A dermoscopic close-up of a skin lesion.
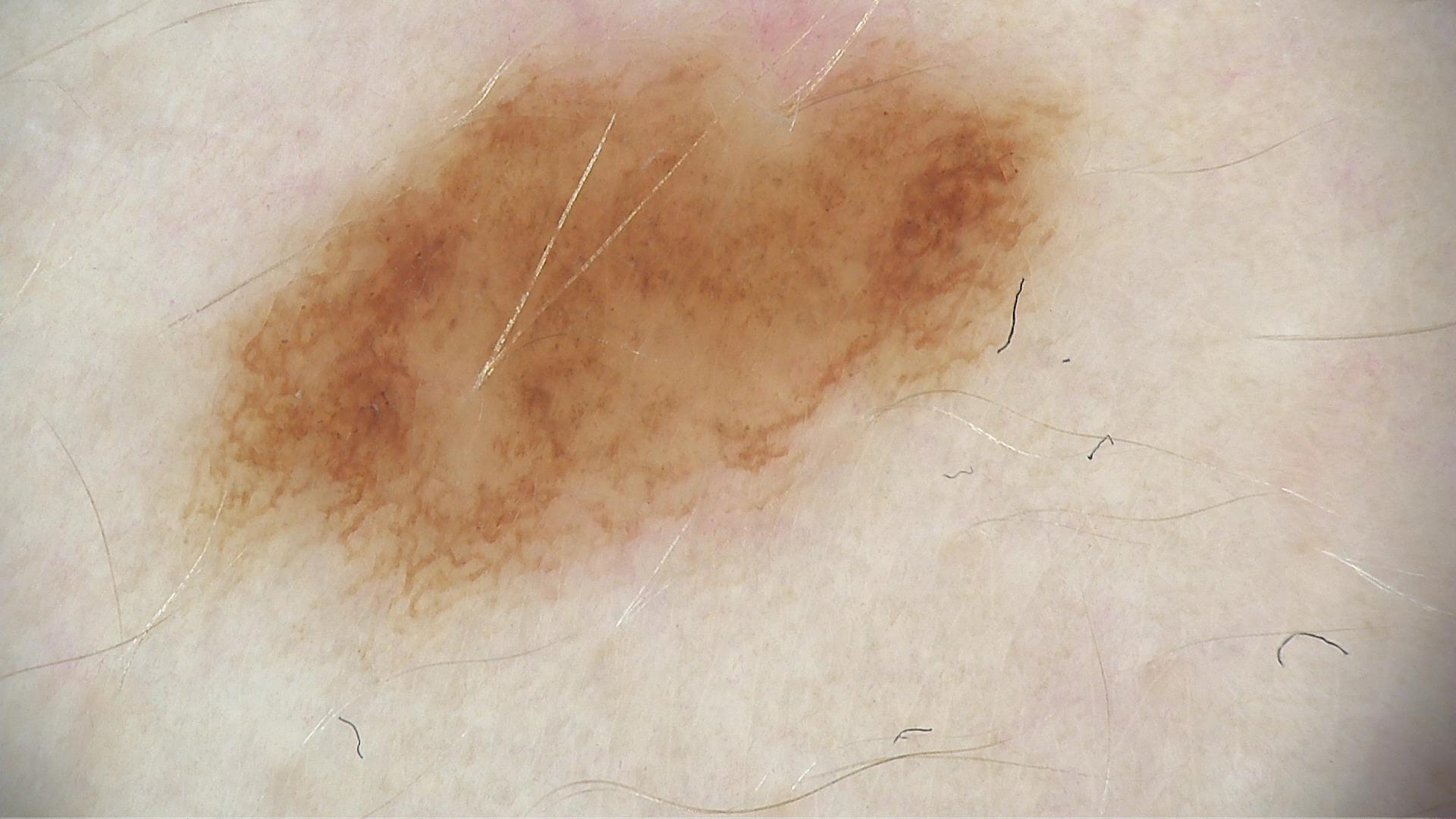class = dysplastic junctional nevus (expert consensus)